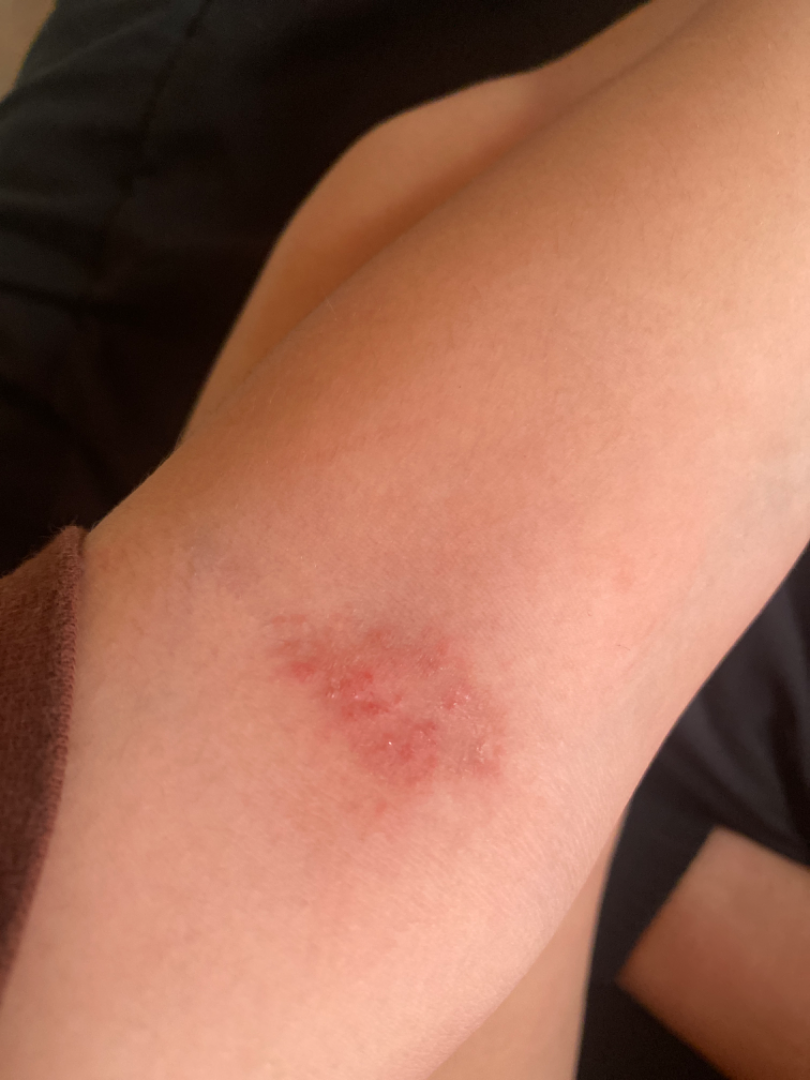Clinical context:
Self-categorized by the patient as a rash. The affected area is the arm. The contributor is 18–29, female. Present for one to three months. The photograph is a close-up of the affected area.
Assessment:
Most consistent with Allergic Contact Dermatitis; possibly Abrasion, scrape, or scab; also consider Eczema.